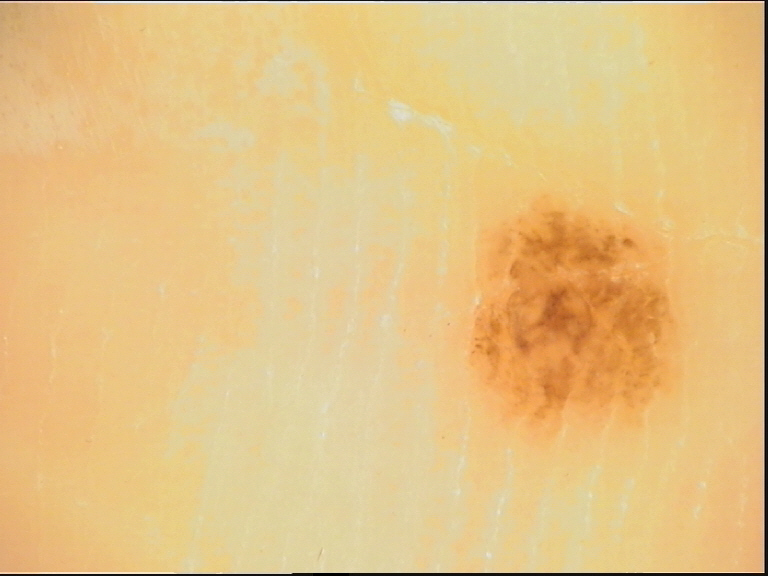label: acral dysplastic junctional nevus (expert consensus)